A dermoscopic photograph of a skin lesion. A female subject aged 73-77.
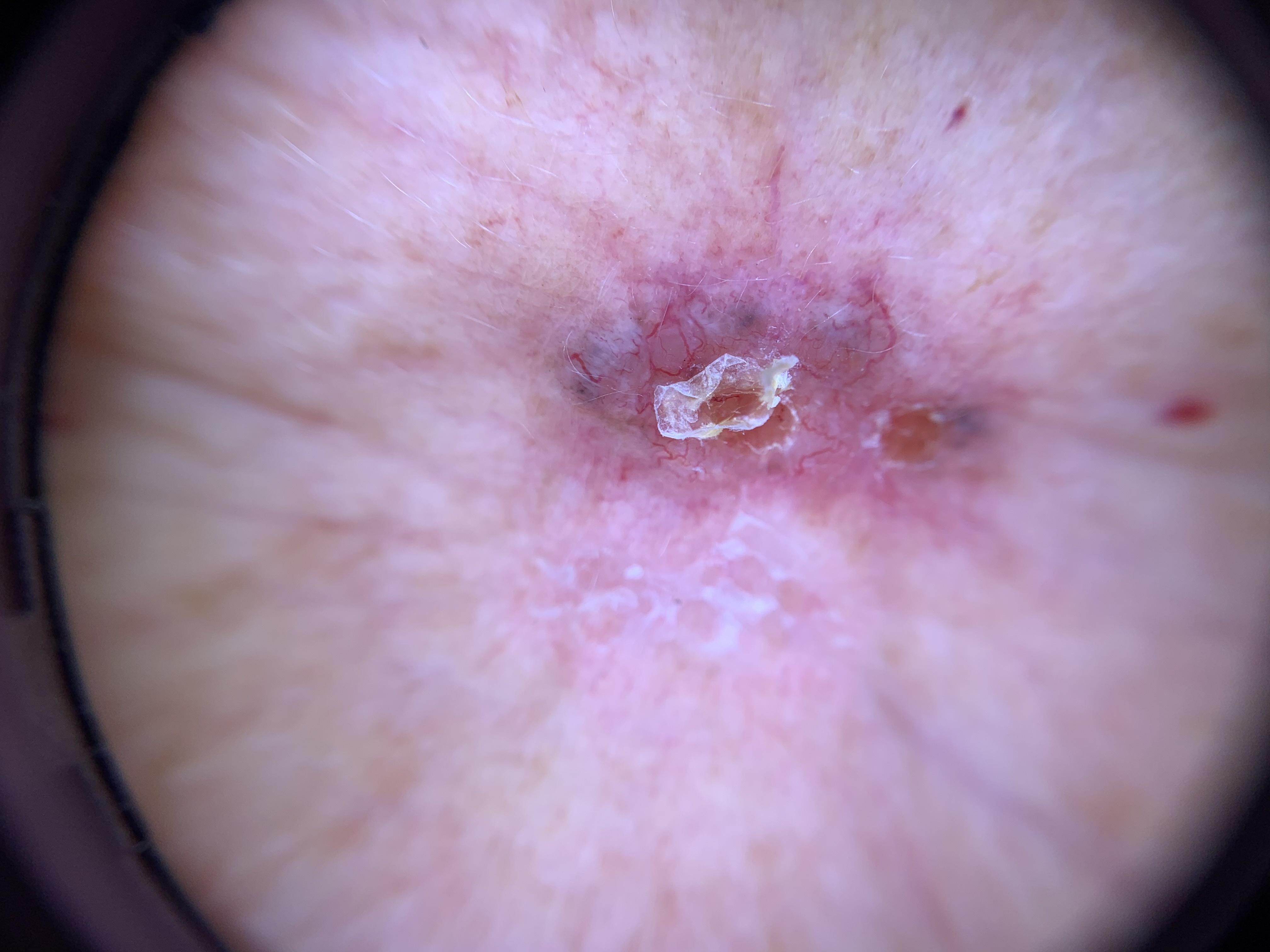Image and clinical context: The lesion is located on the head or neck. Conclusion: Histopathological examination showed a basal cell carcinoma.